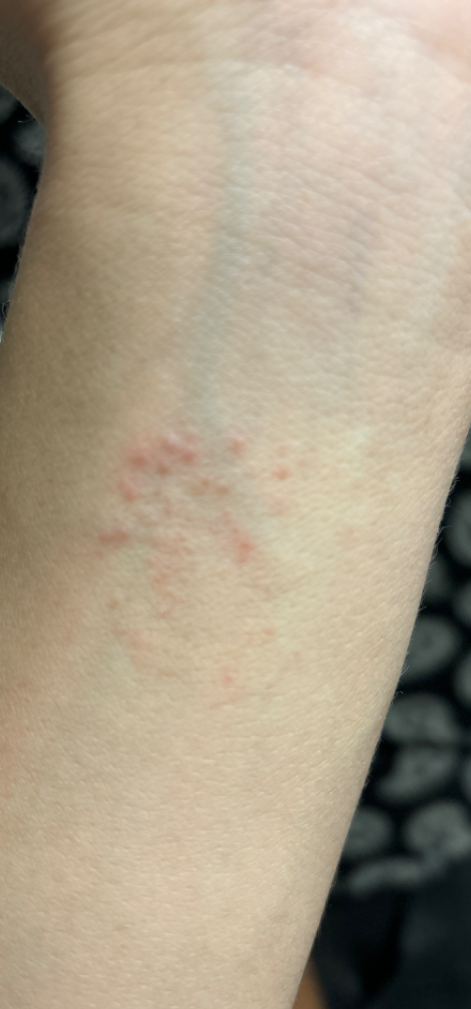location: arm | contributor: male, age 18–29 | shot type: close-up | clinical impression: most consistent with Allergic Contact Dermatitis.